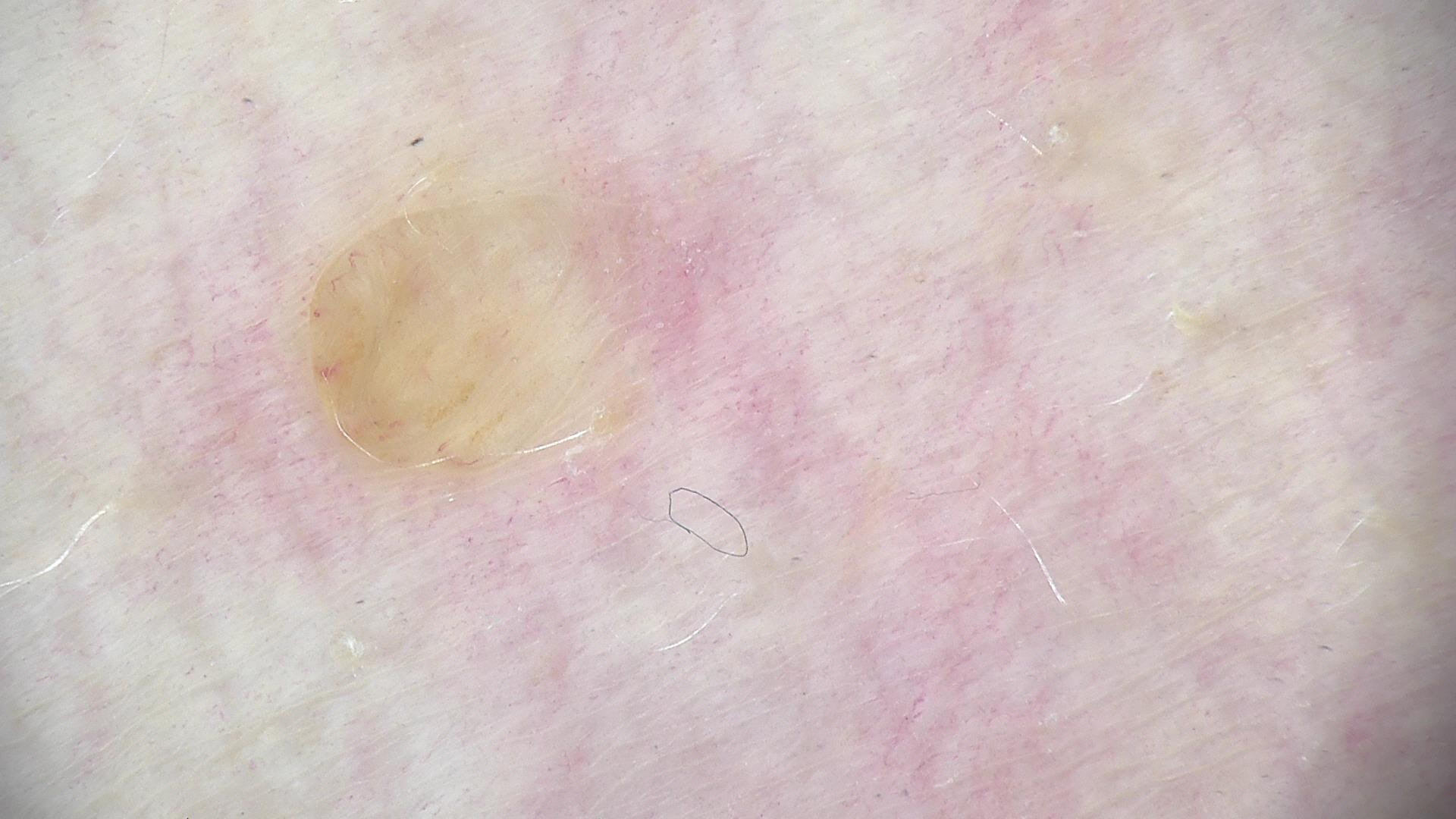Case:
* modality: dermatoscopy
* assessment: dermal nevus (expert consensus)